The lesion is described as raised or bumpy; the lesion is associated with itching and bothersome appearance; the lesion involves the leg, top or side of the foot, back of the hand and arm; present for less than one week; the photograph is a close-up of the affected area — 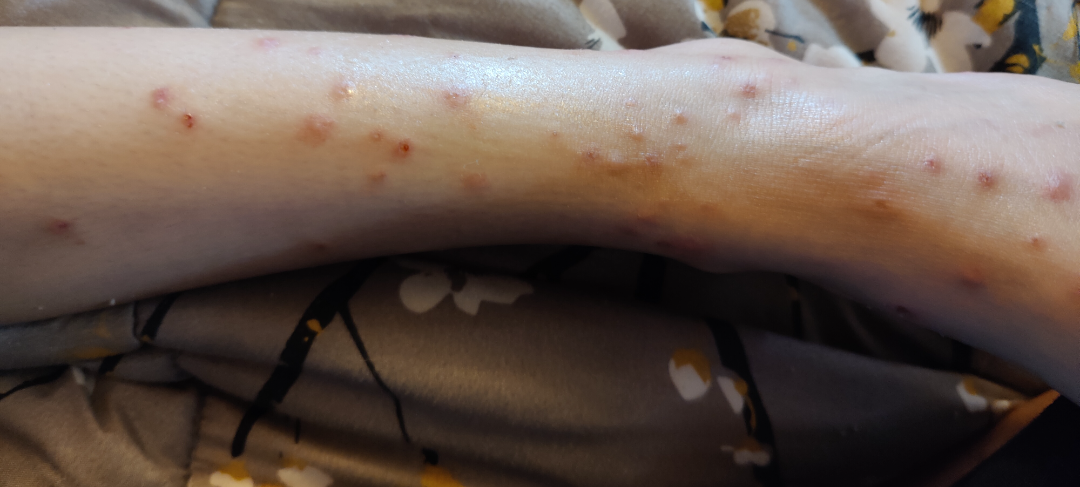{"differential": {"tied_lead": ["Prurigo nodularis", "Insect Bite", "Folliculitis"]}}